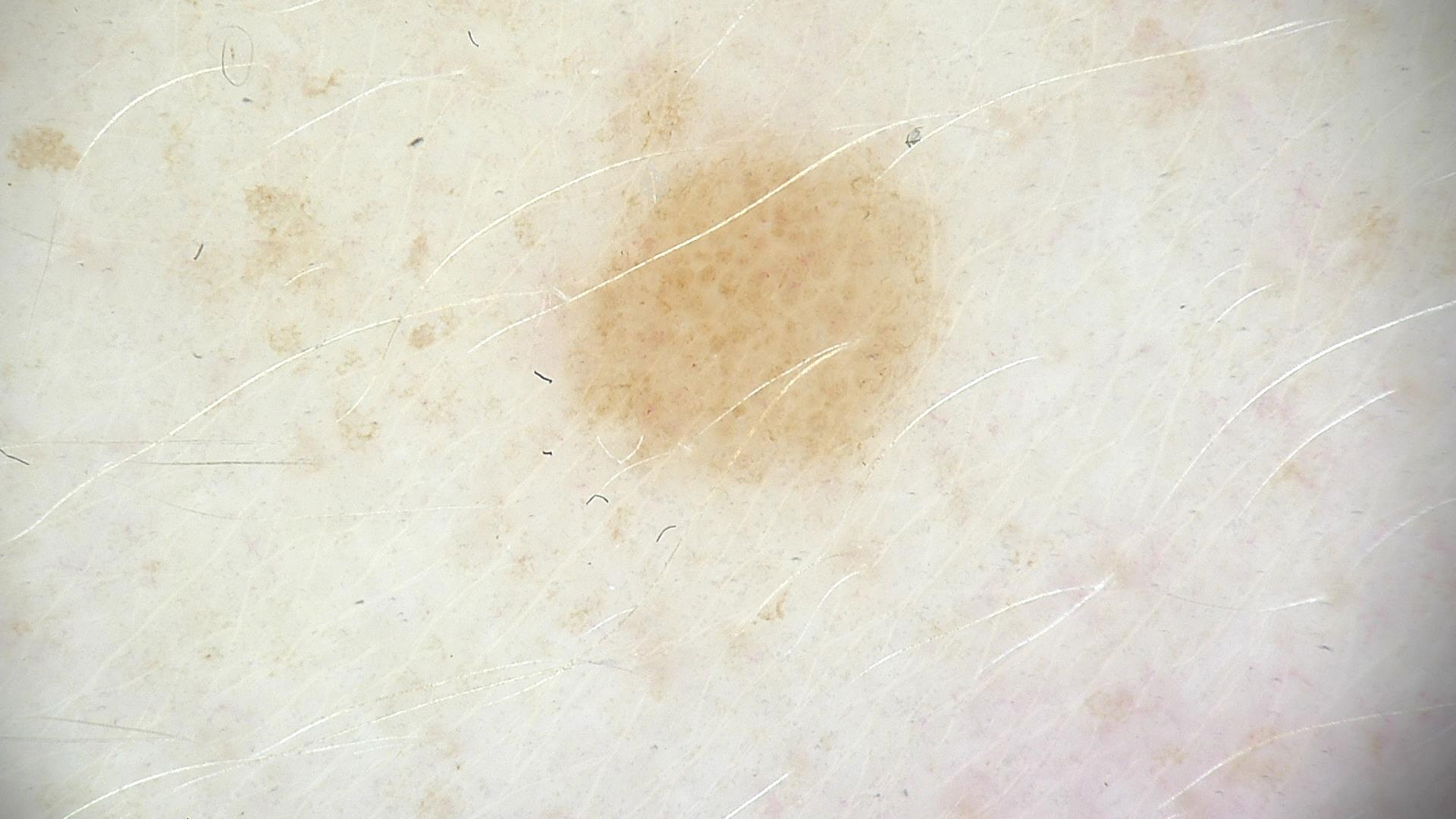The morphology is that of a banal lesion. Diagnosed as a compound nevus.